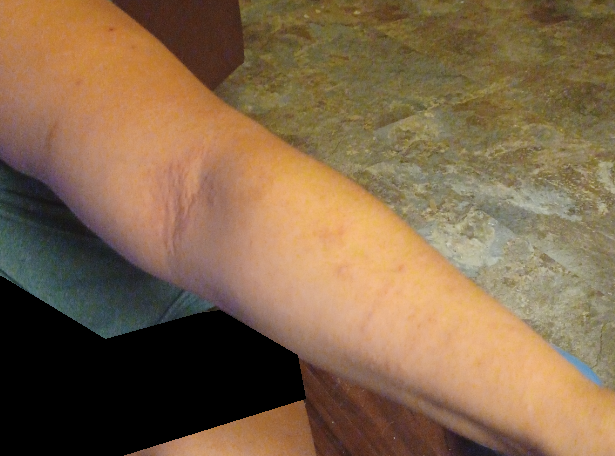| feature | finding |
|---|---|
| assessment | not assessable |